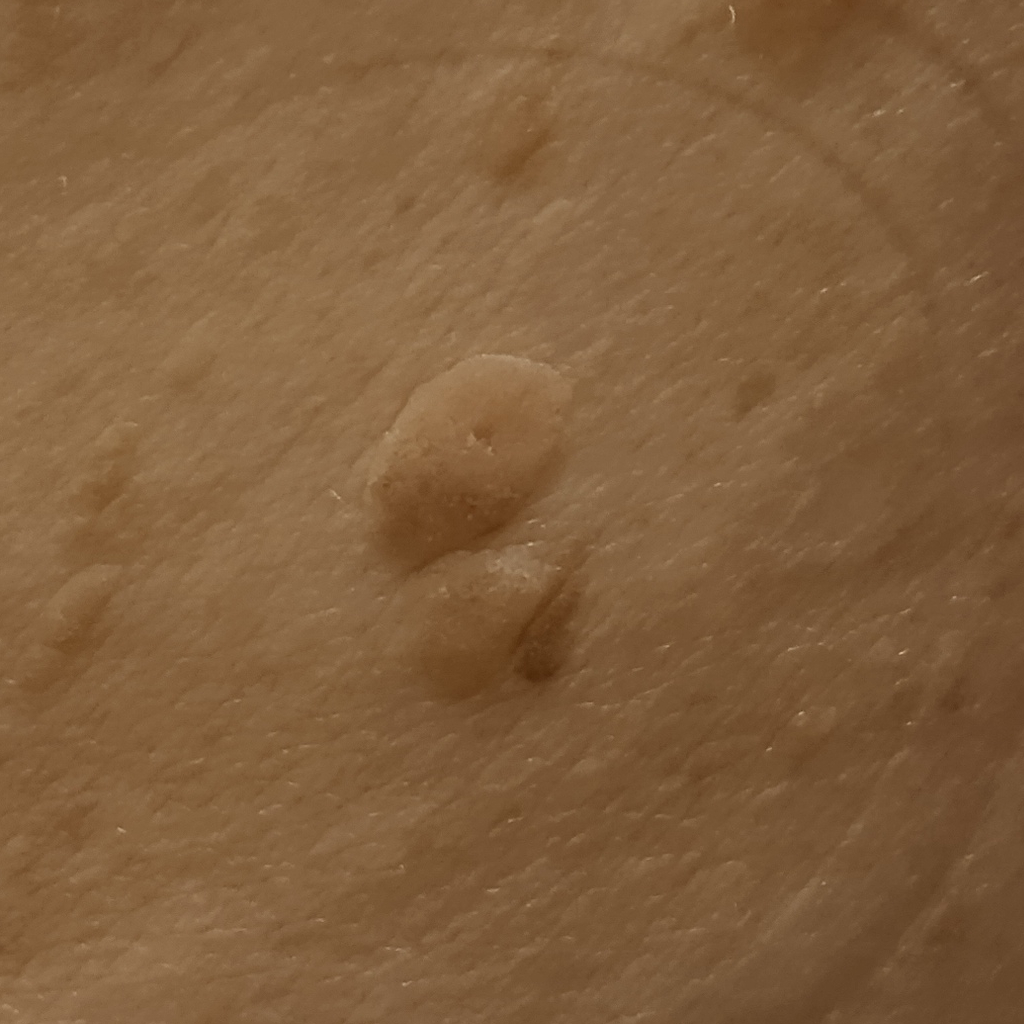The lesion was assessed as a seborrheic keratosis.